A dermoscopy image of a single skin lesion:
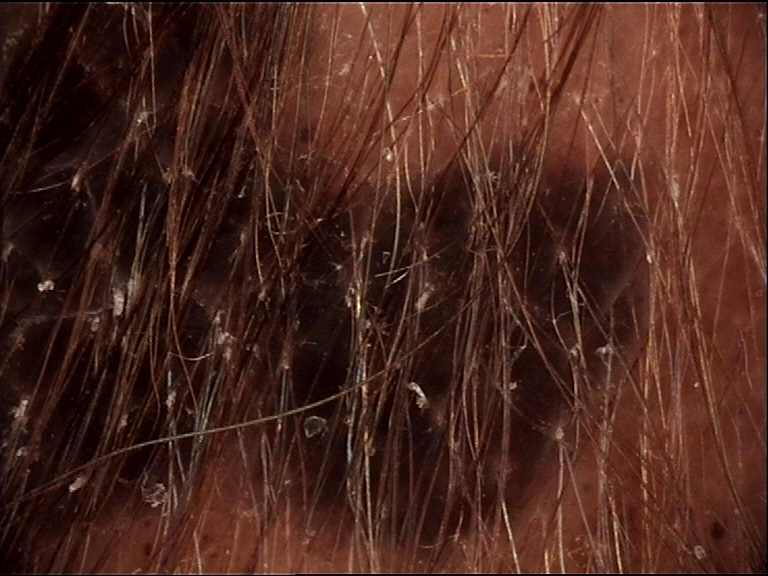- classification — banal
- assessment — congenital compound nevus (expert consensus)